The leg is involved · this image was taken at an angle · the contributor is 30–39, female: 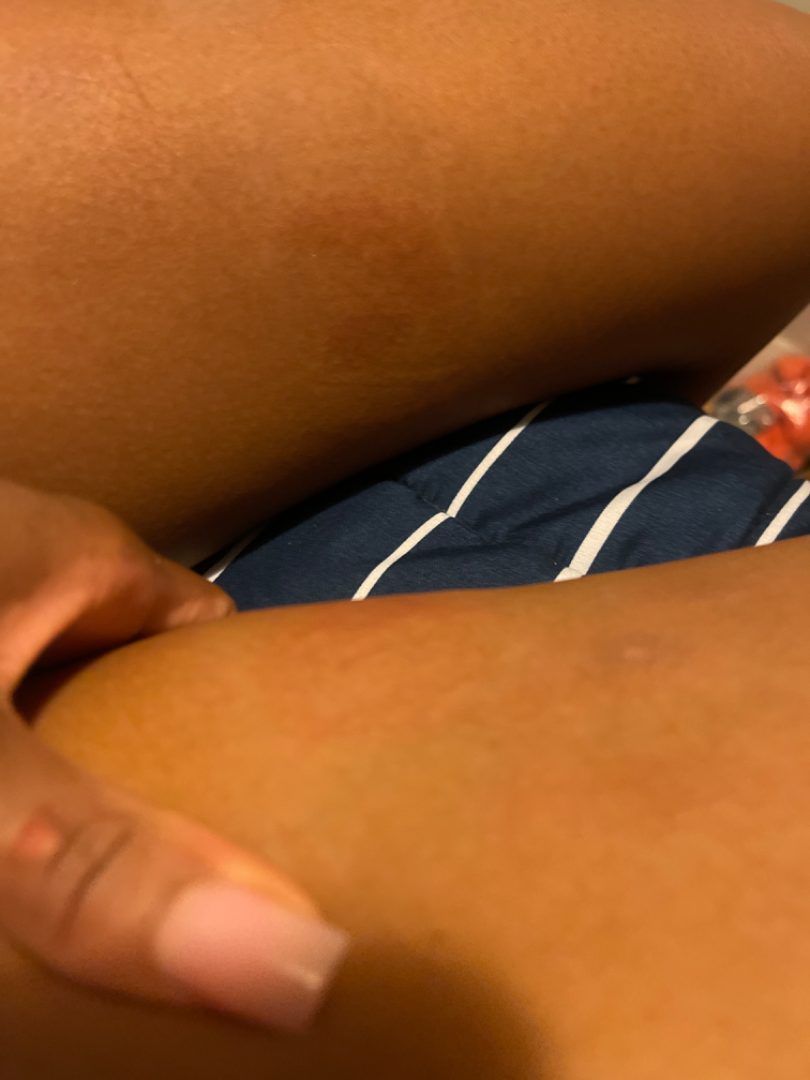Clinical context: Symptoms reported: darkening and itching. The patient notes the lesion is raised or bumpy. The patient described the issue as a rash. Reported duration is one to four weeks. Assessment: On teledermatology review: Allergic Contact Dermatitis (0.27); Eczema (0.23); Acute dermatitis, NOS (0.23); Urticaria (0.17); Tinea (0.10).